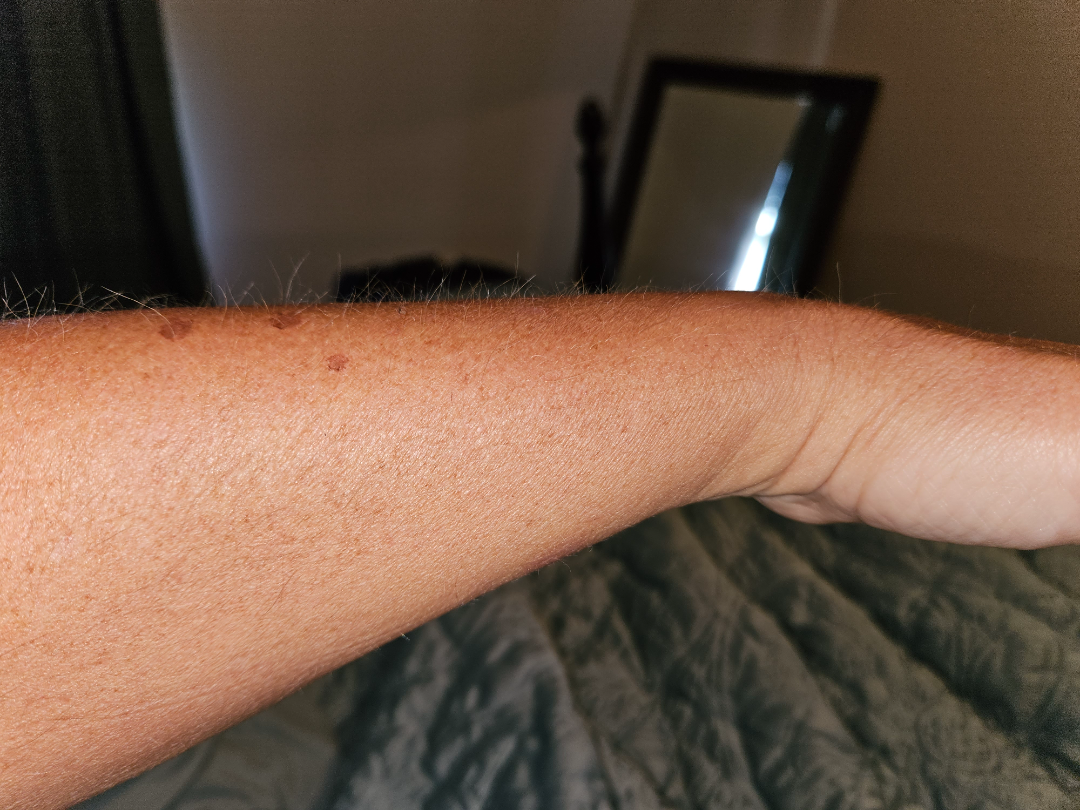The patient described the issue as a rash.
An image taken at an angle.
Reported duration is one to four weeks.
The lesion is described as flat.
The subject is a female aged 50–59.
The affected area is the back of the hand and arm.
On remote dermatologist review: Burn of forearm (33%); Abrasion, scrape, or scab (33%); Actinic Keratosis (33%).